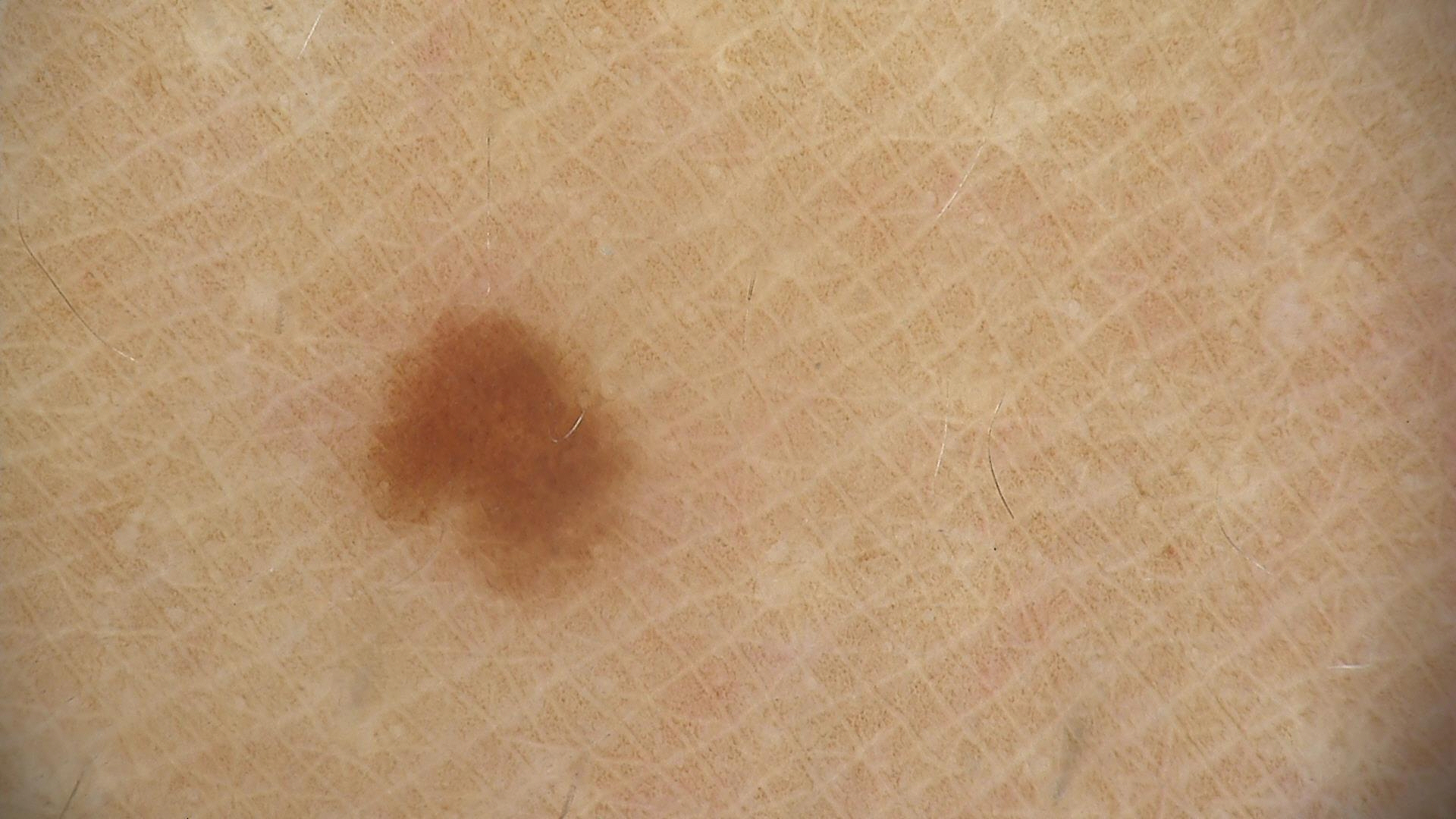assessment: dysplastic junctional nevus (expert consensus).